This is a dermoscopic photograph of a skin lesion:
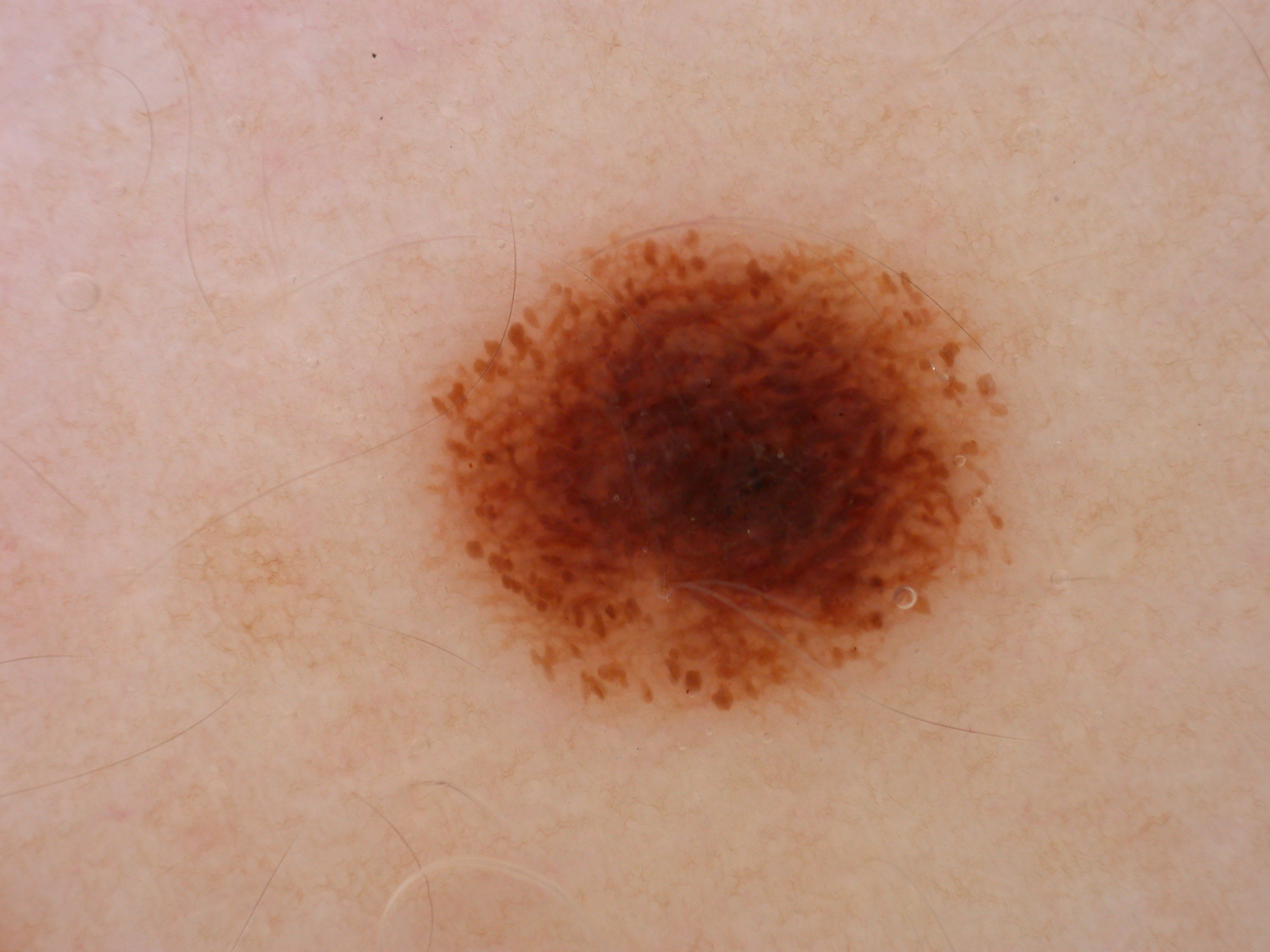With coordinates (x1, y1, x2, y2), the lesion spans [421,221,1012,719].
On dermoscopy, the lesion shows globules and pigment network; no negative network, streaks, or milia-like cysts.
The lesion occupies roughly 18% of the field.
Clinically diagnosed as a melanocytic nevus.